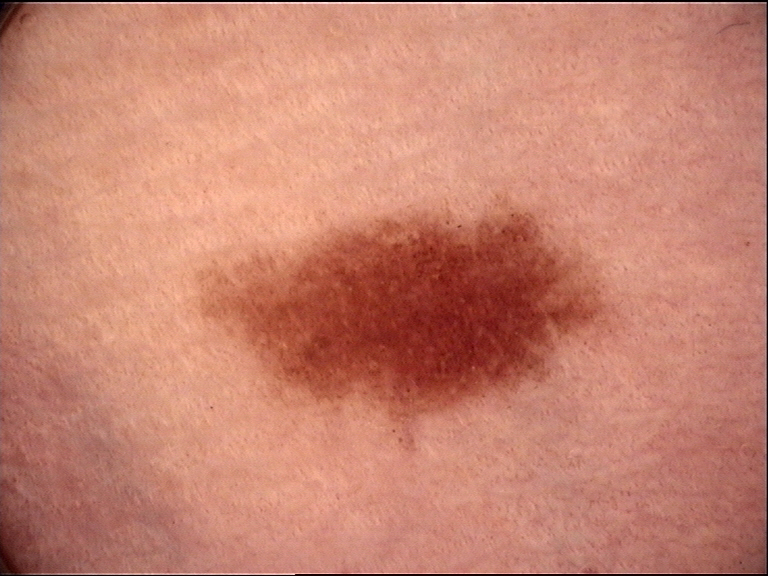A dermatoscopic image of a skin lesion. Diagnosed as a dysplastic junctional nevus.